A dermatoscopic image of a skin lesion: 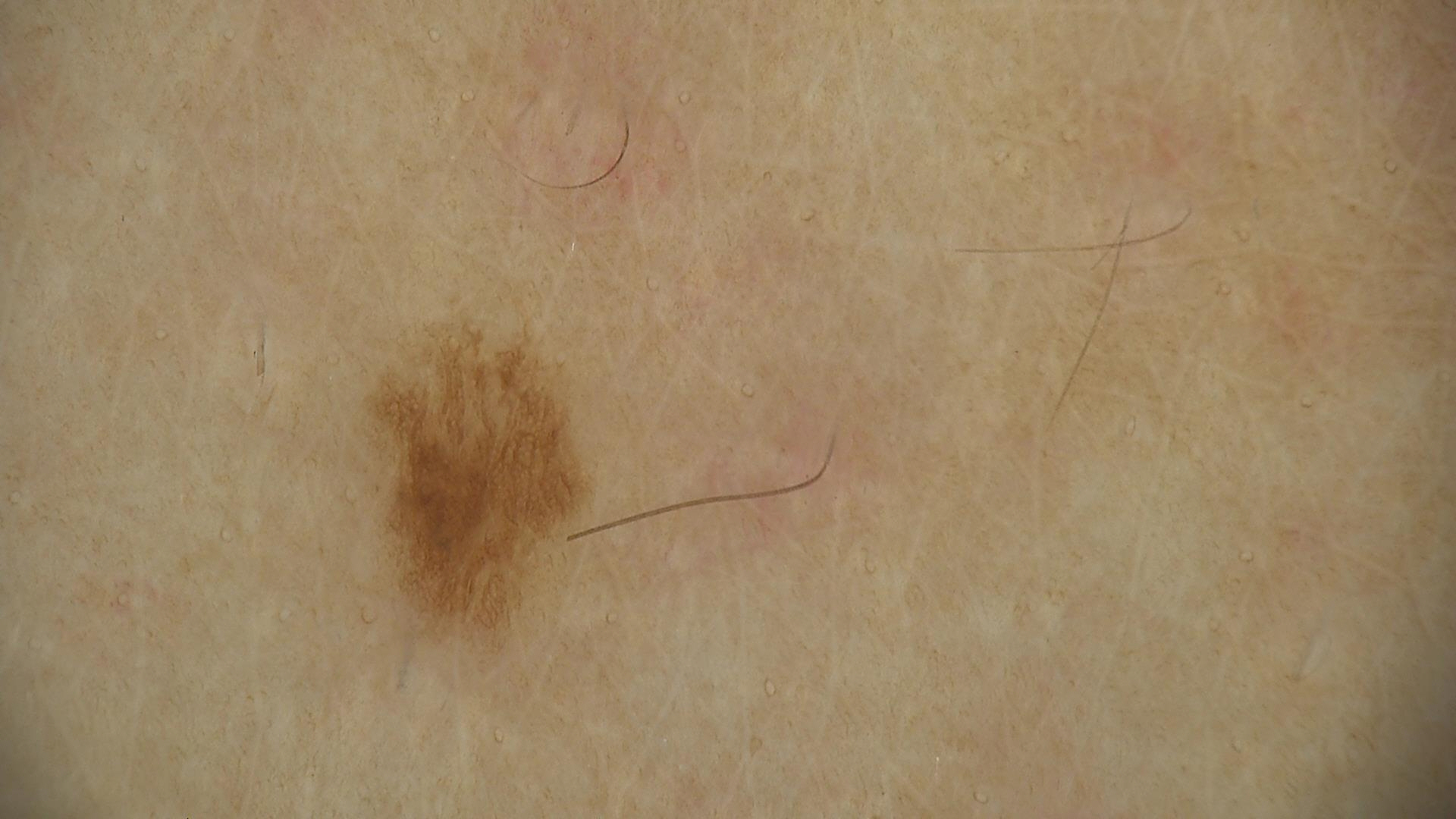The diagnosis was a benign lesion — a dysplastic junctional nevus.